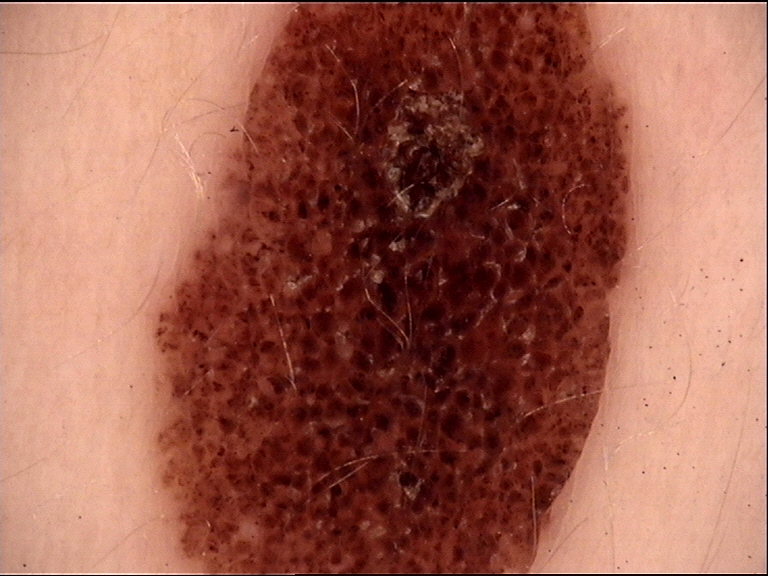category: banal | assessment: congenital compound nevus (expert consensus).